A dermoscopic close-up of a skin lesion.
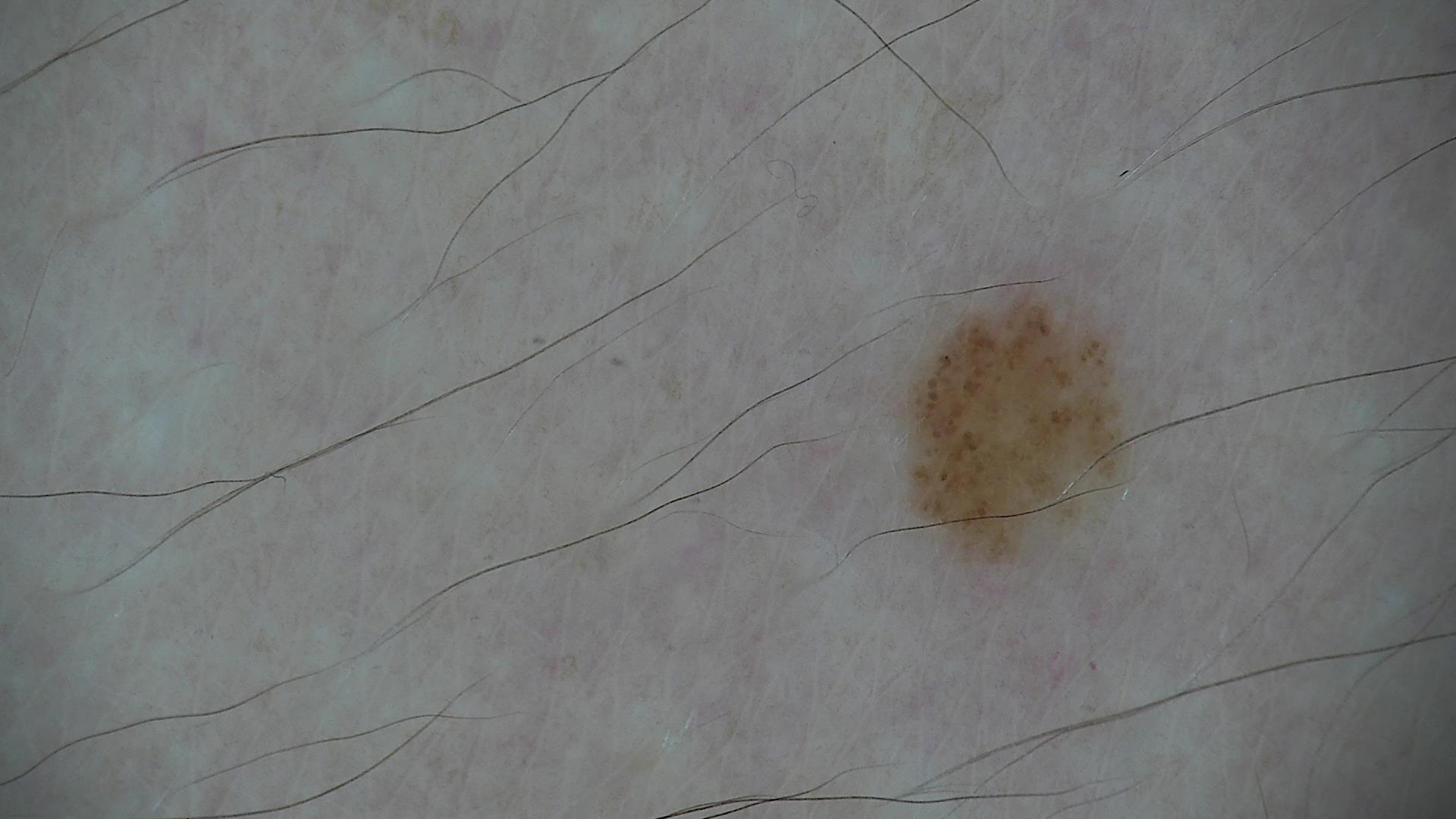Impression: Consistent with a dysplastic junctional nevus.